A dermoscopic image of a skin lesion: 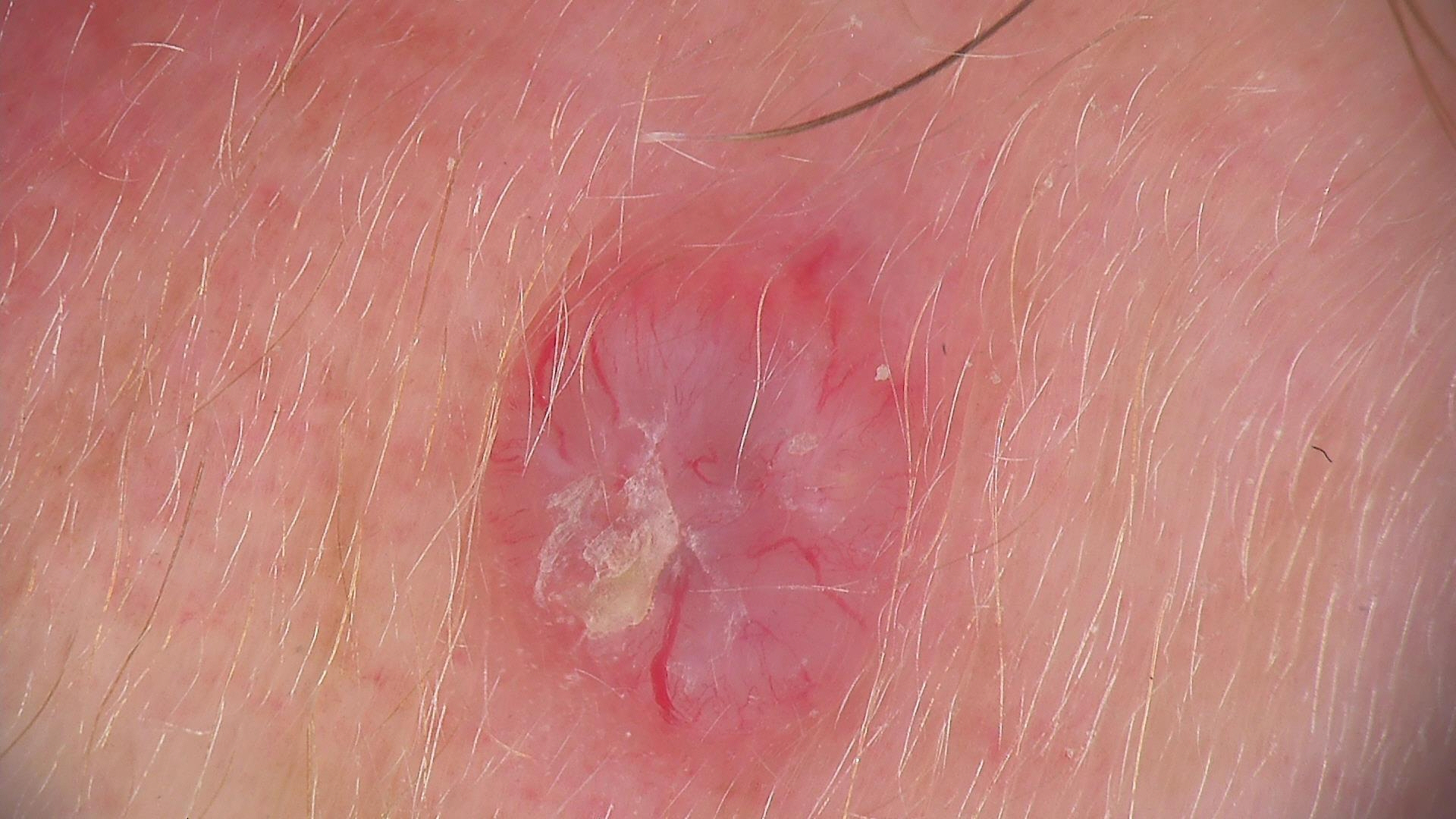This is a keratinocytic lesion. The biopsy diagnosis was a malignancy — a basal cell carcinoma.